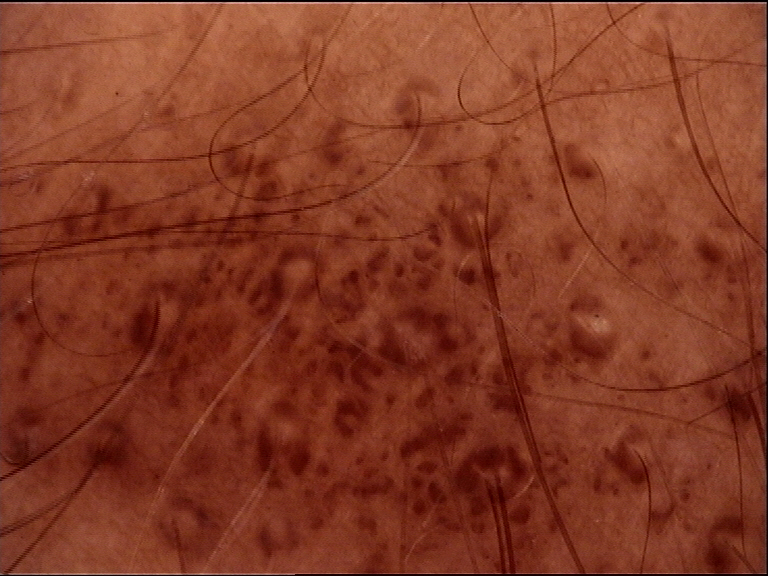Conclusion:
The diagnostic label was a congenital junctional nevus.